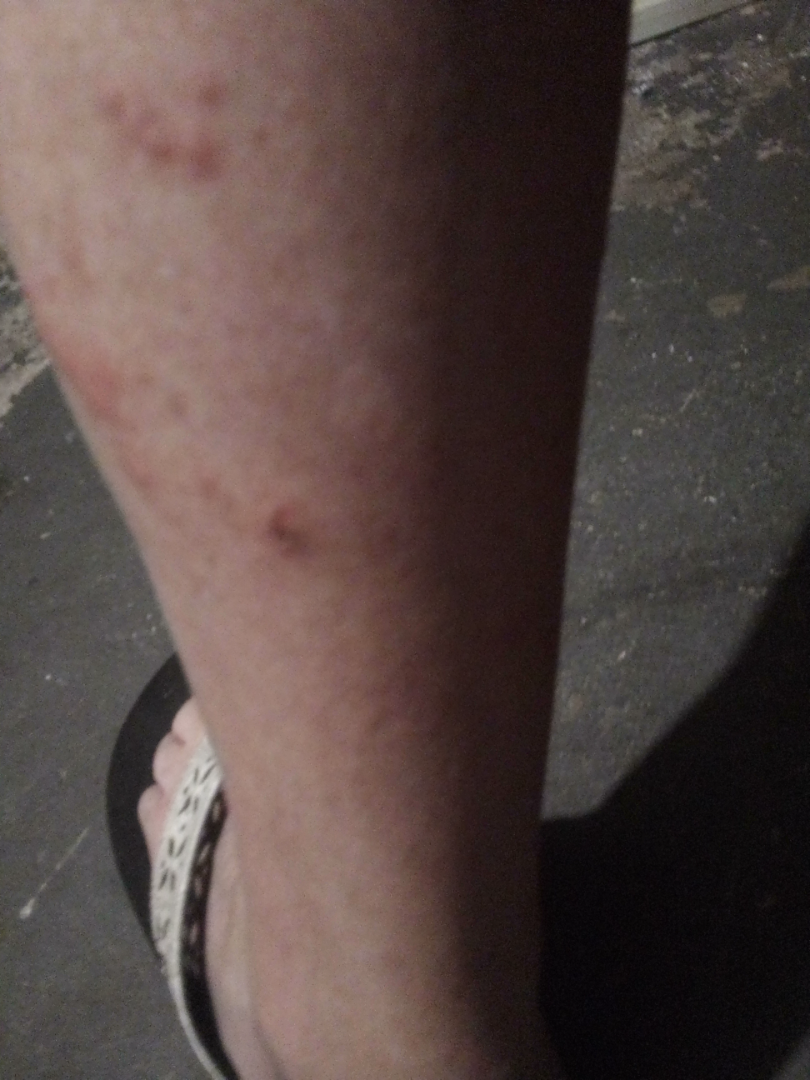The skin findings could not be characterized from the image.
No constitutional symptoms were reported.
The affected area is the head or neck, arm, leg and back of the torso.
Close-up view.
The patient reports the lesion is fluid-filled and raised or bumpy.
Self-categorized by the patient as a rash.
Symptoms reported: itching.